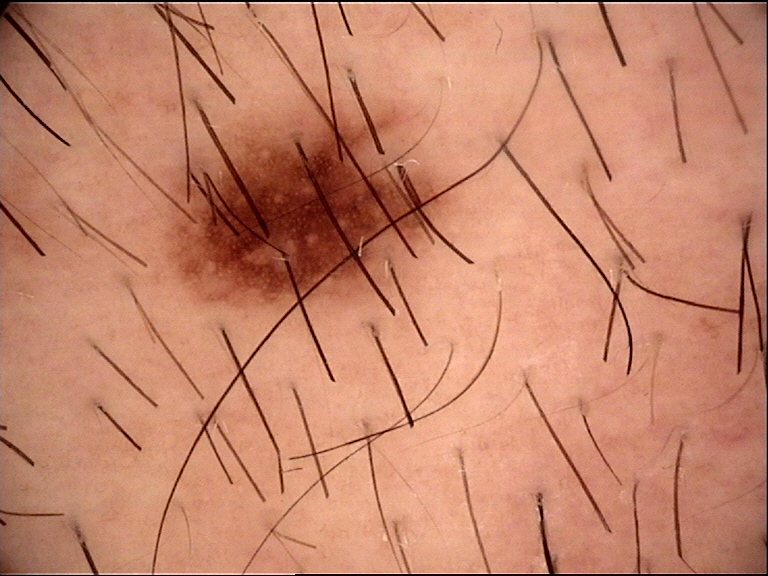* modality — dermatoscopy
* label — dysplastic junctional nevus (expert consensus)